The lesion involves the front of the torso · the contributor reports pain, itching, burning, bothersome appearance and darkening · this image was taken at an angle · the patient described the issue as a rash · present for less than one week · the patient is a female aged 18–29: 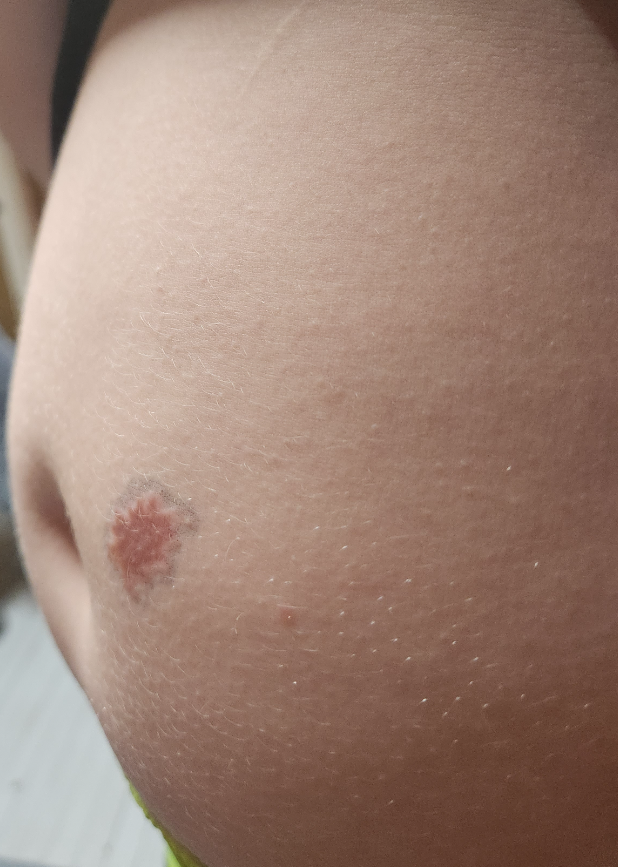differential:
  leading:
    - Melanocytic Nevus
  considered:
    - Atypical Nevus
    - Melanoma